Contact-polarized dermoscopy of a skin lesion. Per the chart, no melanoma in first-degree relatives and no prior melanoma. The patient is Fitzpatrick skin type IV. A female subject aged 53-57.
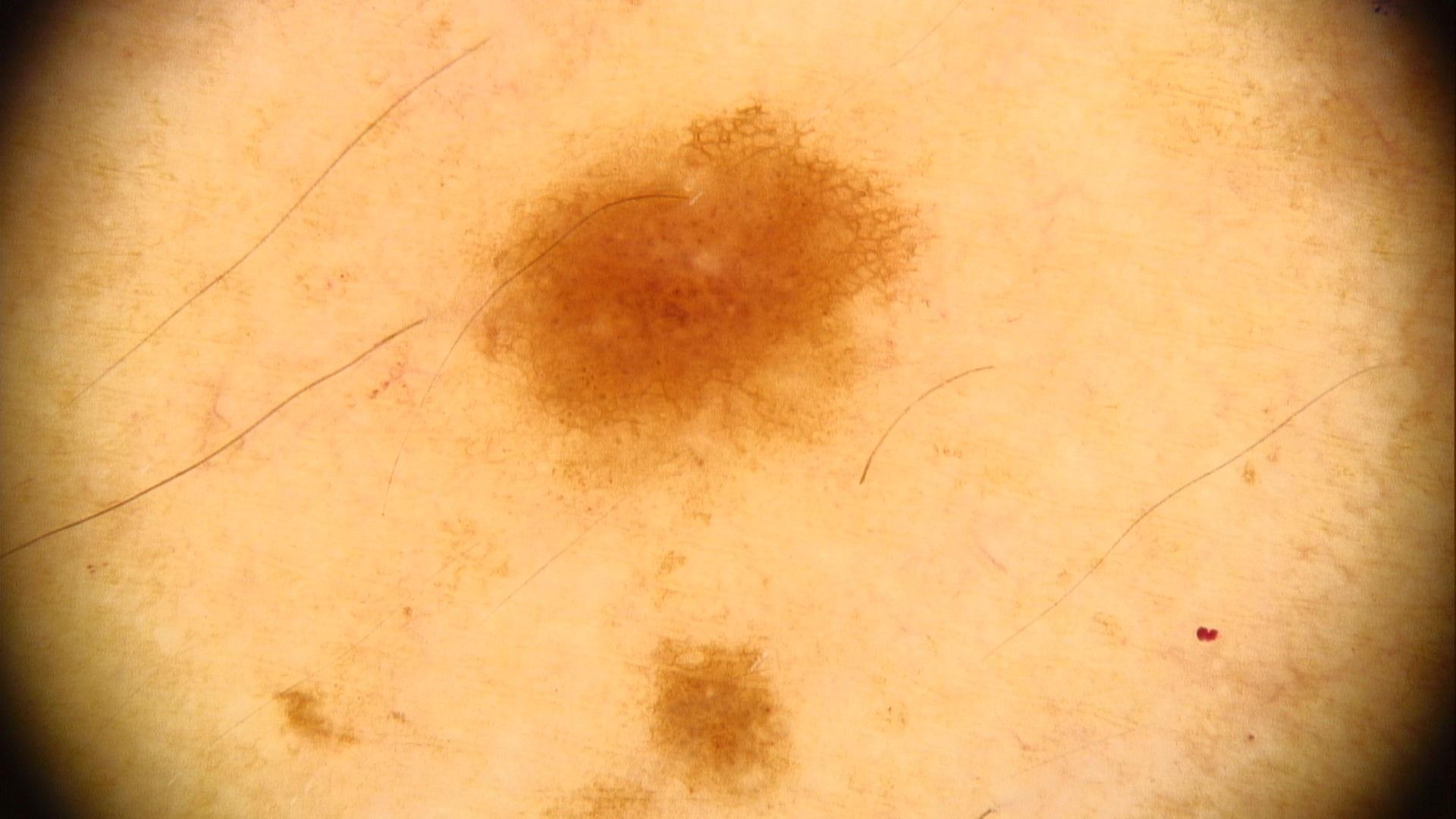The lesion is located on an upper extremity. Consistent with a nevus.